The patient is 30–39, female · FST III; human graders estimated 2 on the MST · close-up view — 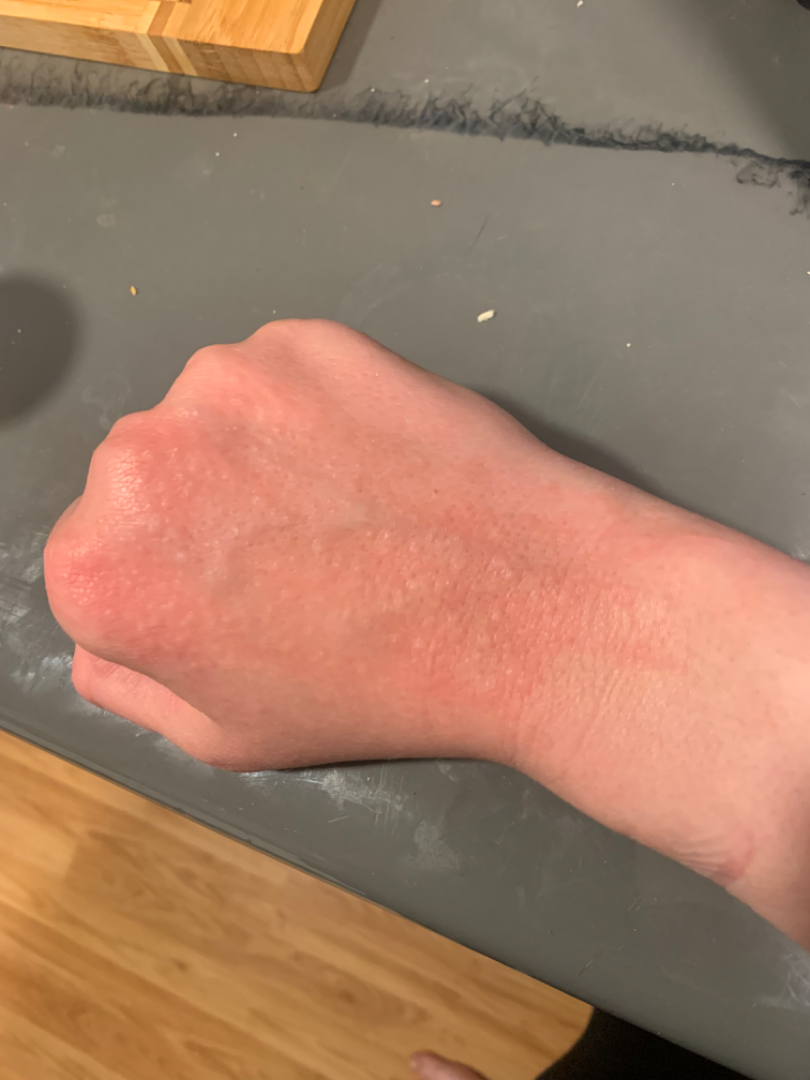Case summary:
– diagnostic considerations · Photodermatitis, Allergic Contact Dermatitis and Irritant Contact Dermatitis were considered with similar weight